Dermoscopy of a skin lesion.
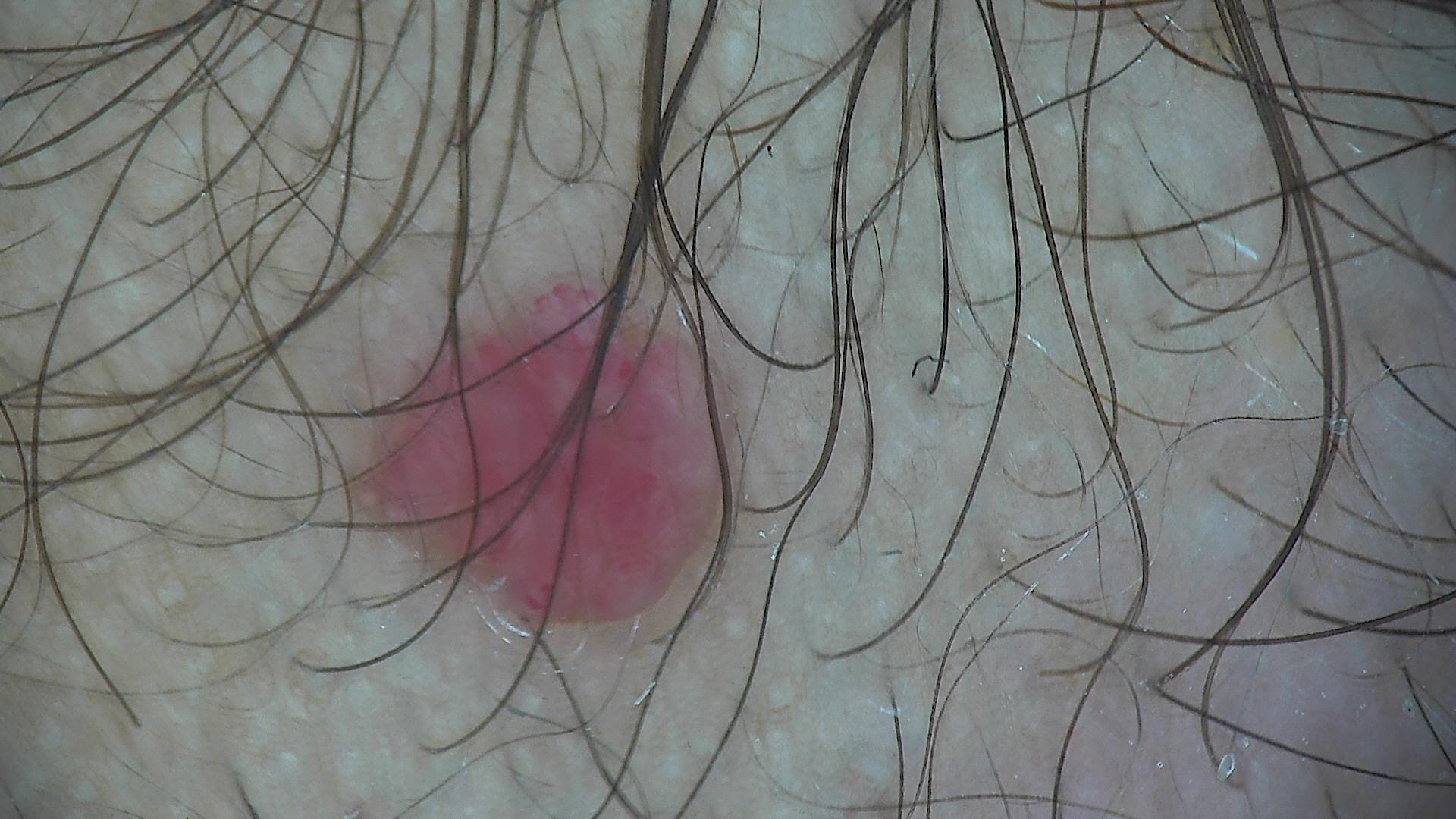assessment = hemangioma (expert consensus).